The patient is a male aged 30–39, this image was taken at an angle:
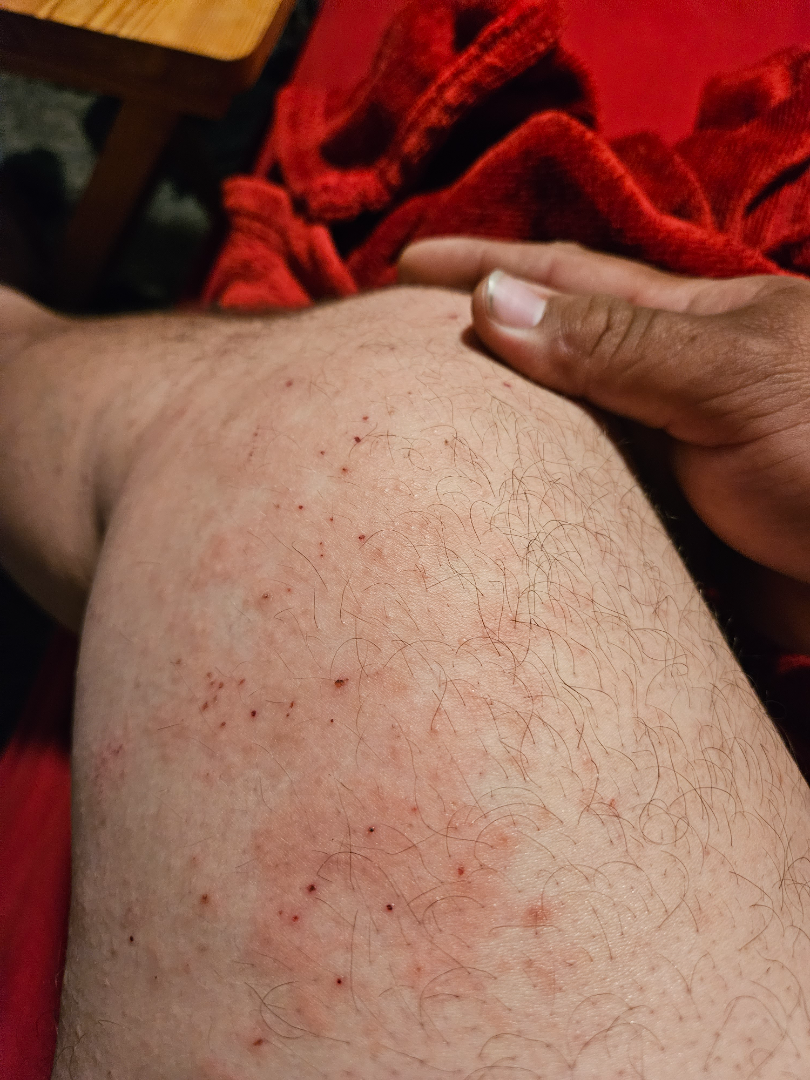dermatologist impression = in keeping with Acute and chronic dermatitis.